A dermatoscopic image of a skin lesion.
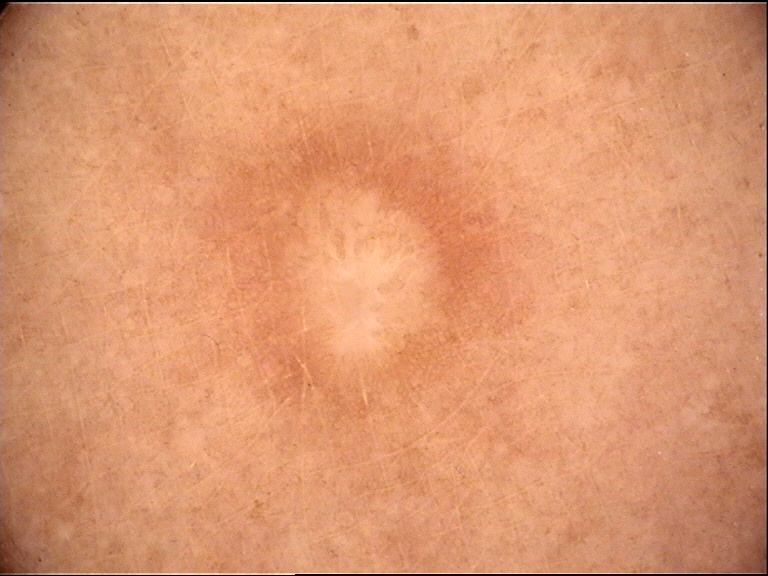class = dermatofibroma (expert consensus).